A dermoscopic image of a skin lesion. A female patient in their mid- to late 20s — 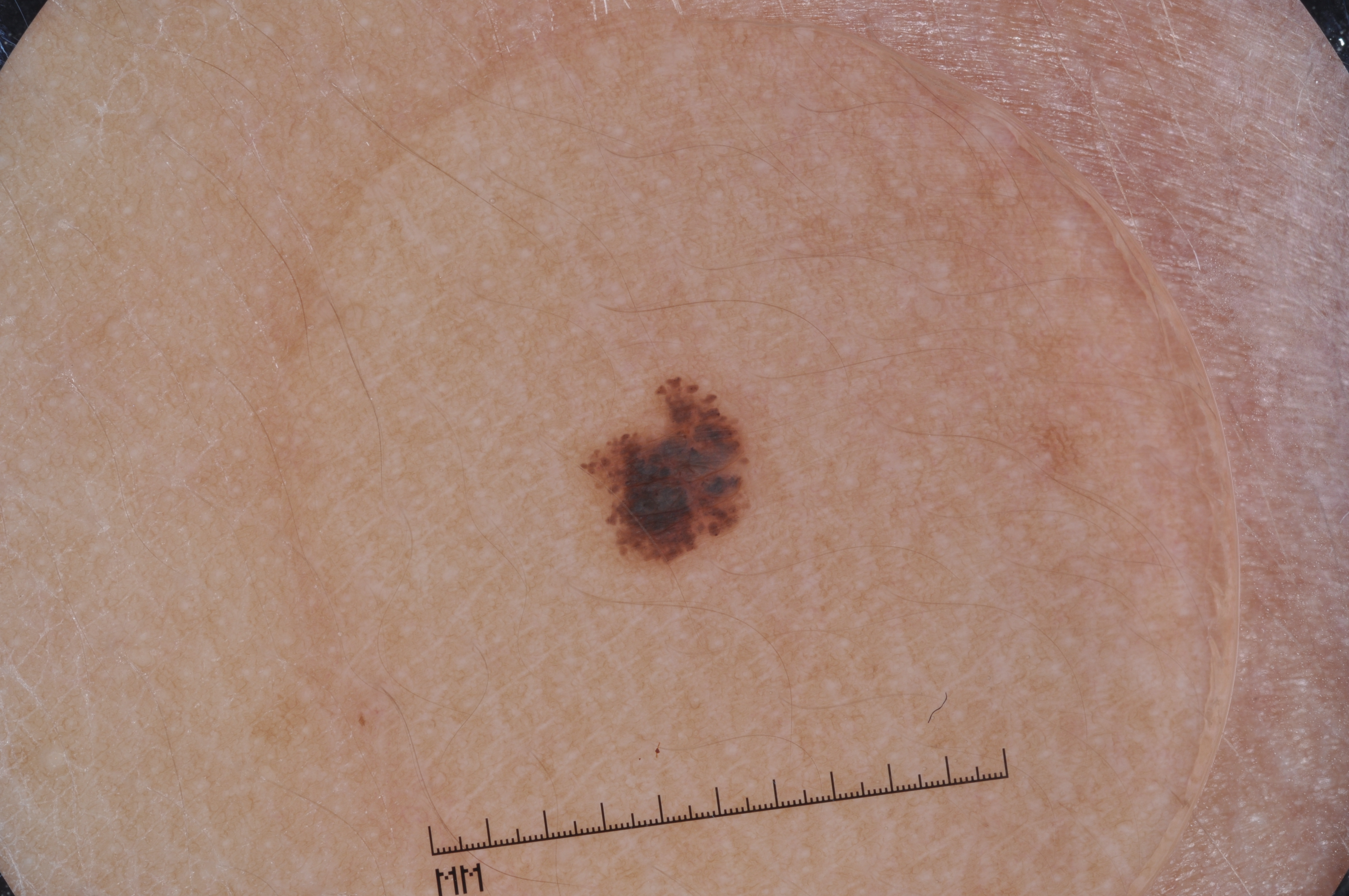Image and clinical context:
Dermoscopic examination shows streaks. A small lesion within a wider field of skin. As (left, top, right, bottom), the lesion's extent is bbox=[590, 385, 759, 560].
Conclusion:
Expert review diagnosed this as a melanocytic nevus.